A dermoscopy image of a single skin lesion.
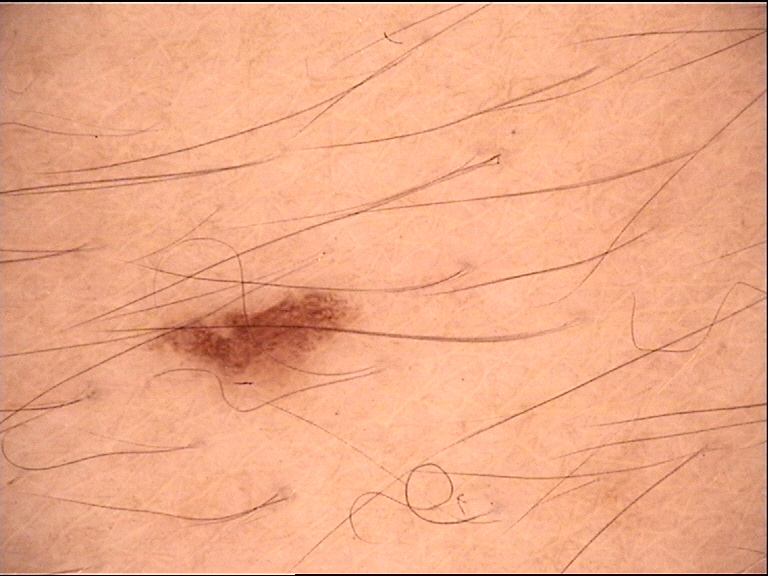Labeled as a banal lesion — a junctional nevus.